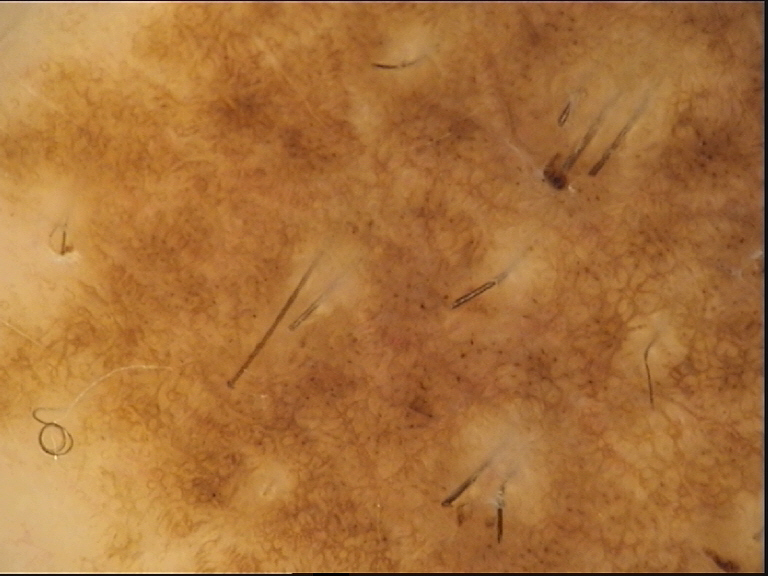A dermoscopic image of a skin lesion. The diagnostic label was a banal lesion — a congenital compound nevus.